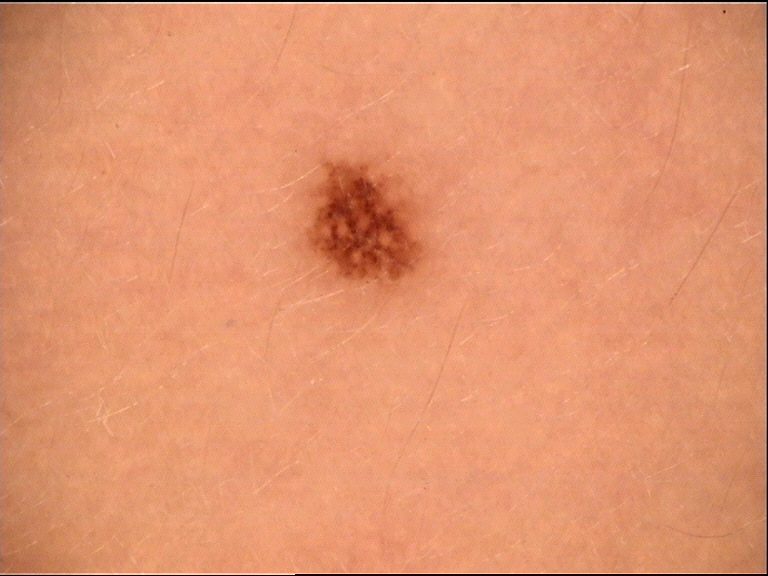  image: dermatoscopy
  lesion_type:
    main_class: banal
    pattern: junctional
  diagnosis:
    name: junctional nevus
    code: jb
    malignancy: benign
    super_class: melanocytic
    confirmation: expert consensus